A dermoscopic image of a skin lesion.
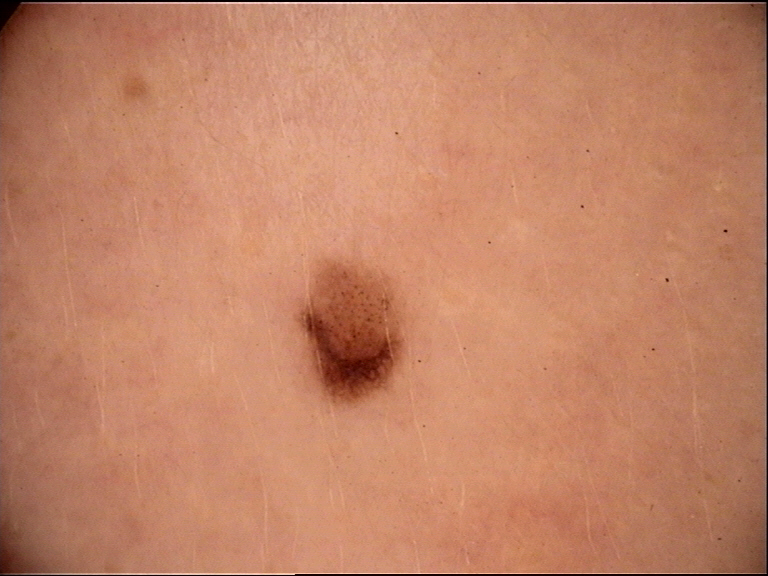Impression: The diagnostic label was a benign lesion — a dysplastic junctional nevus.